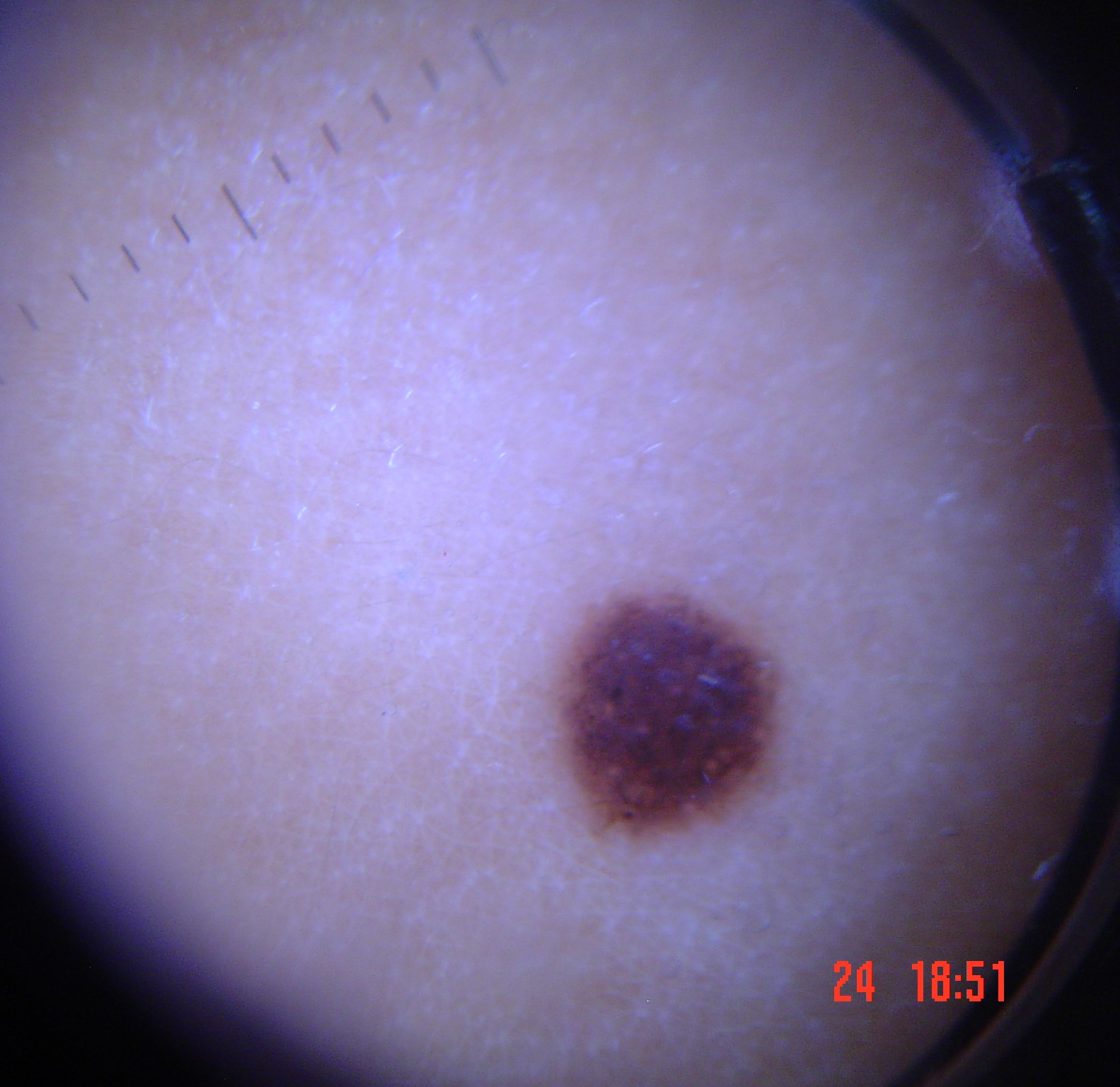A dermoscopy image of a single skin lesion. Diagnosed as a benign lesion — a dysplastic compound nevus.